A dermoscopic photograph of a skin lesion.
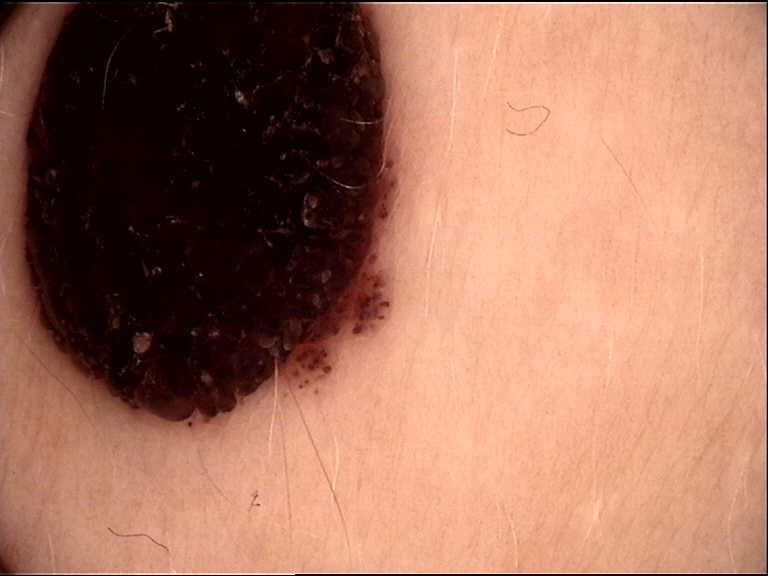Summary:
This is a banal lesion.
Conclusion:
Classified as a dermal nevus.